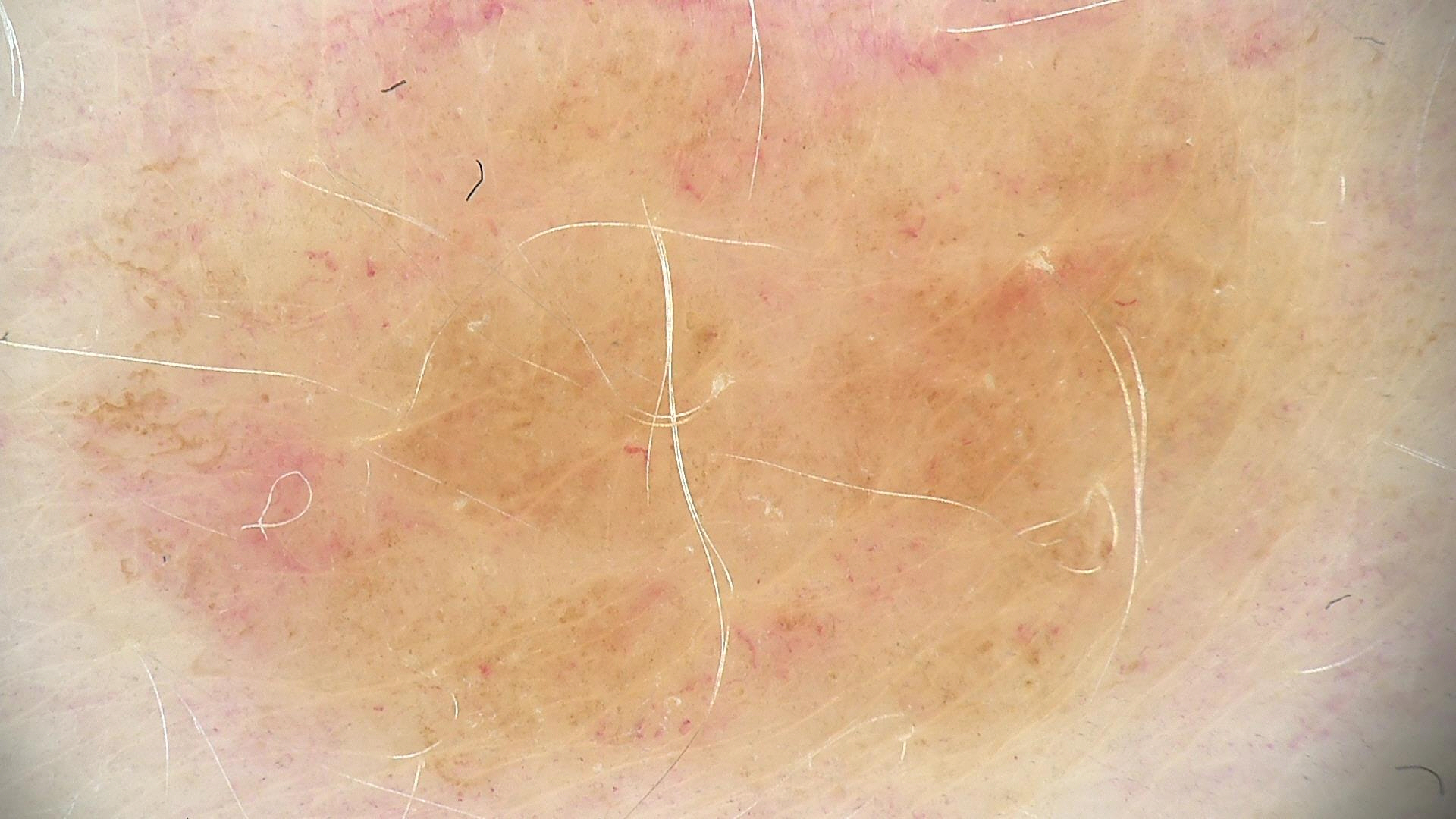A skin lesion imaged with a dermatoscope. The diagnostic label was a benign lesion — a dysplastic junctional nevus.